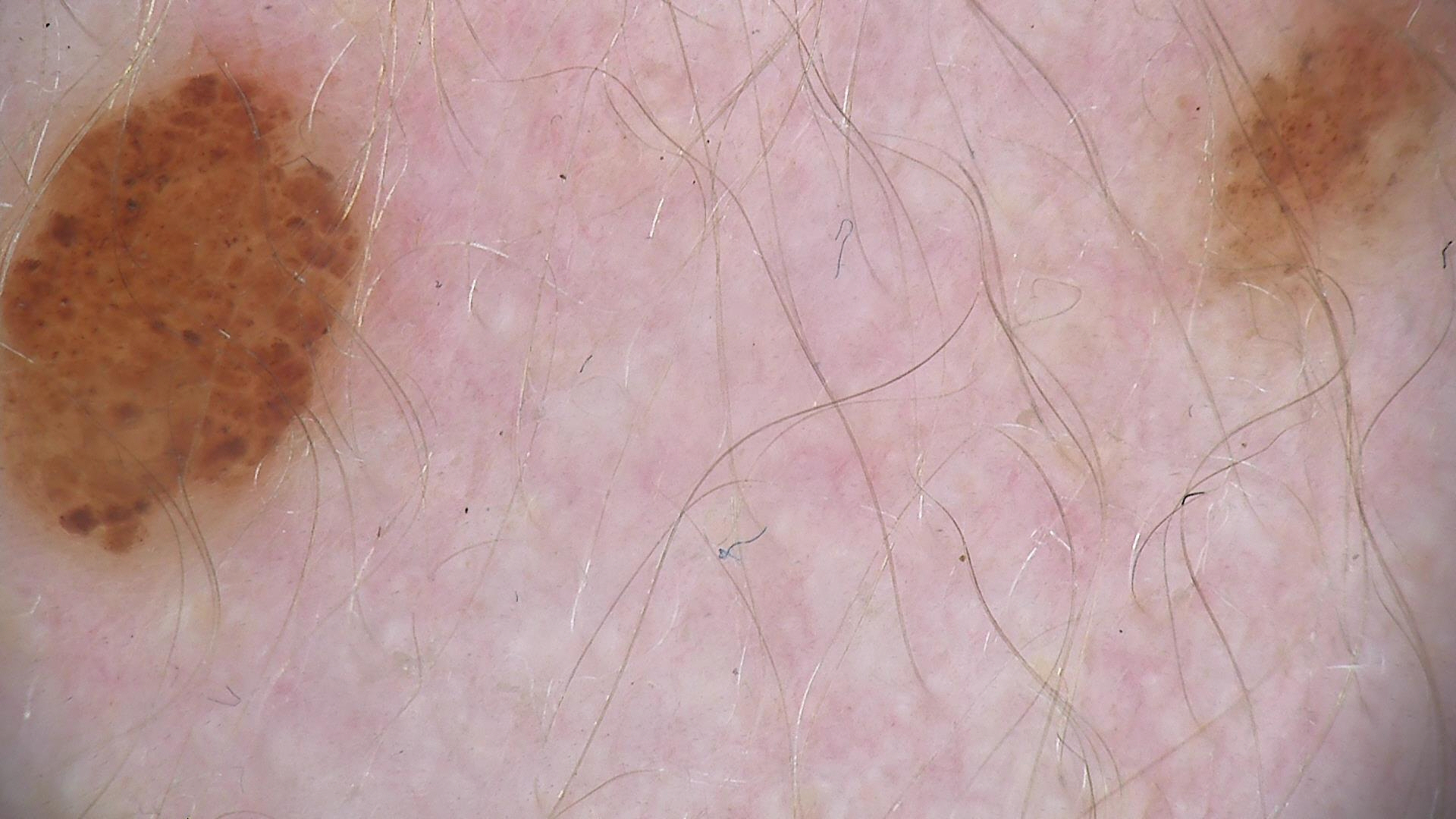Case:
- diagnosis: compound nevus (expert consensus)